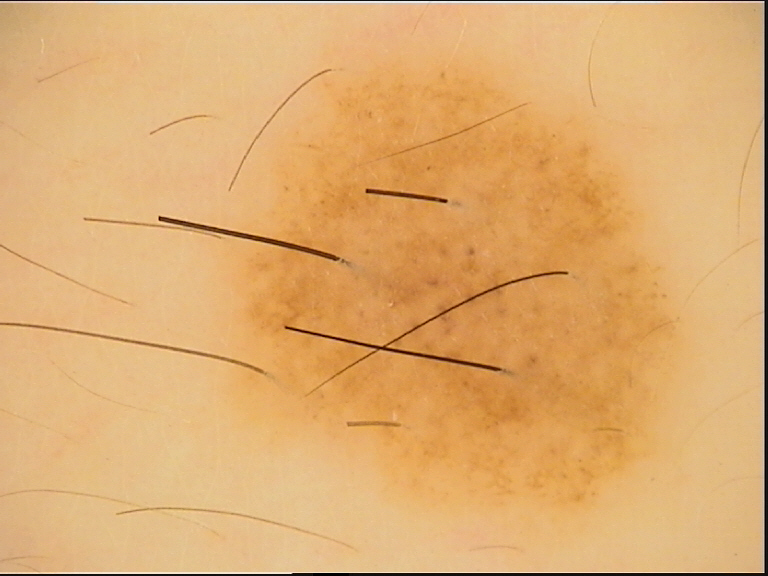• modality · dermoscopy
• class · dysplastic compound nevus (expert consensus)